The photo was captured at an angle · the affected area is the top or side of the foot · the contributor is 30–39, male: 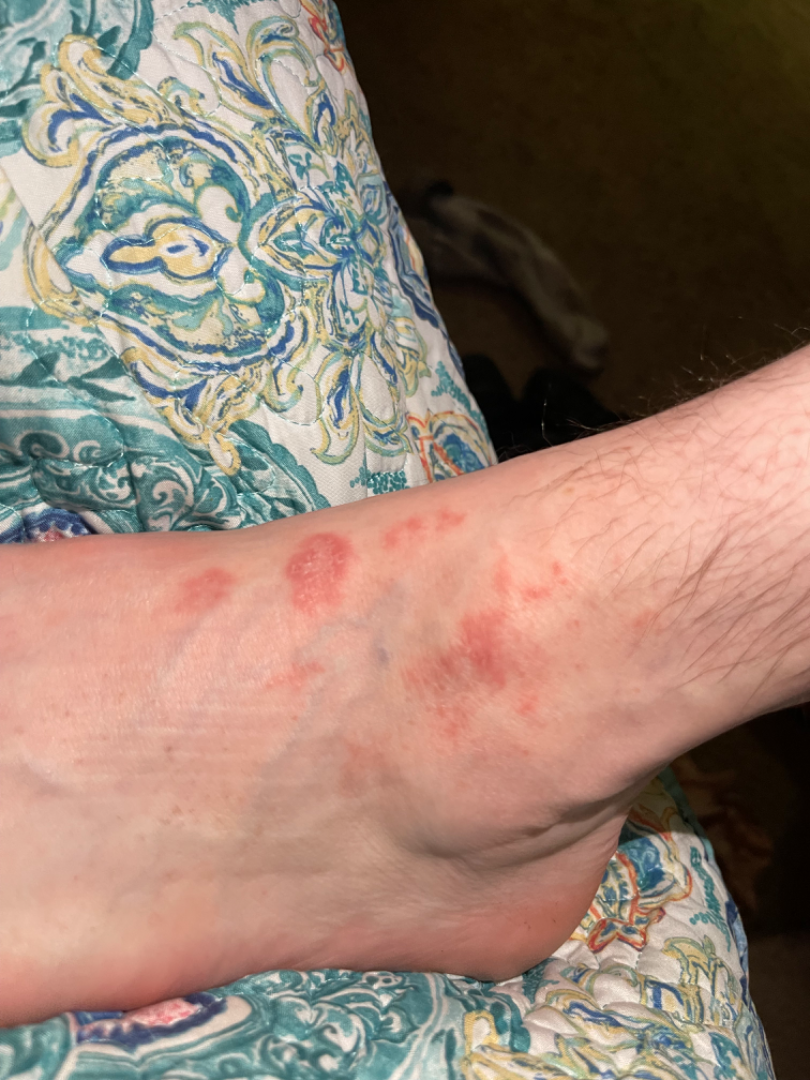Notes:
– assessment — could not be assessed
– surface texture — raised or bumpy
– self-categorized as — a rash
– history — one to four weeks